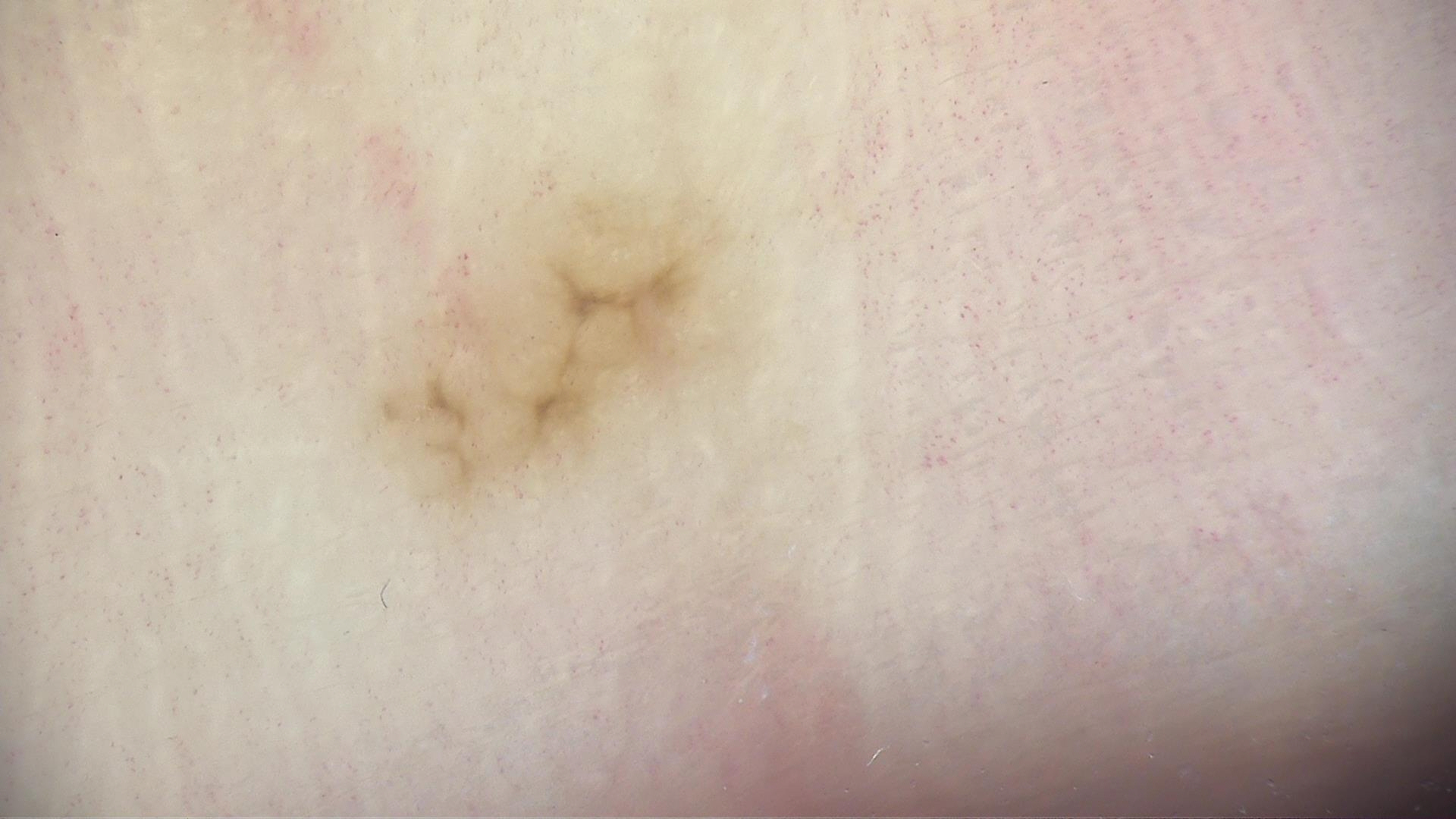A dermoscopic close-up of a skin lesion. Labeled as a benign lesion — an acral dysplastic junctional nevus.